A skin lesion imaged with a dermatoscope.
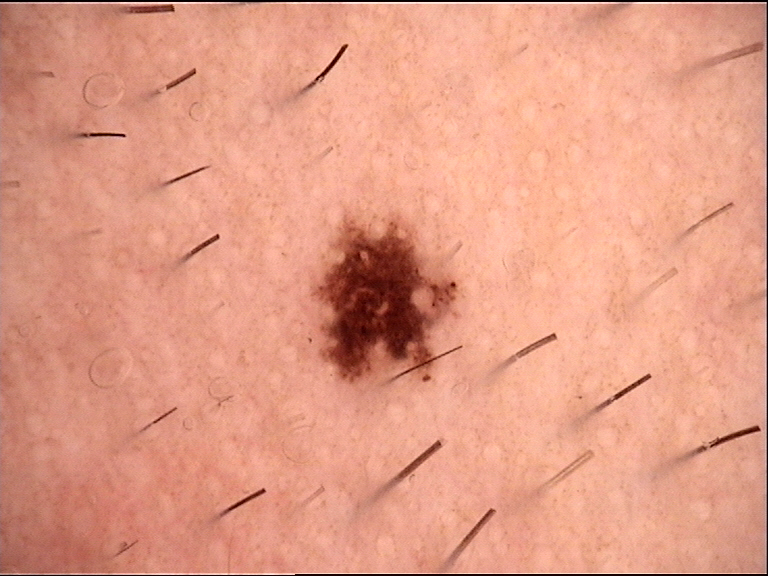{"diagnosis": {"name": "dysplastic junctional nevus", "code": "jd", "malignancy": "benign", "super_class": "melanocytic", "confirmation": "expert consensus"}}